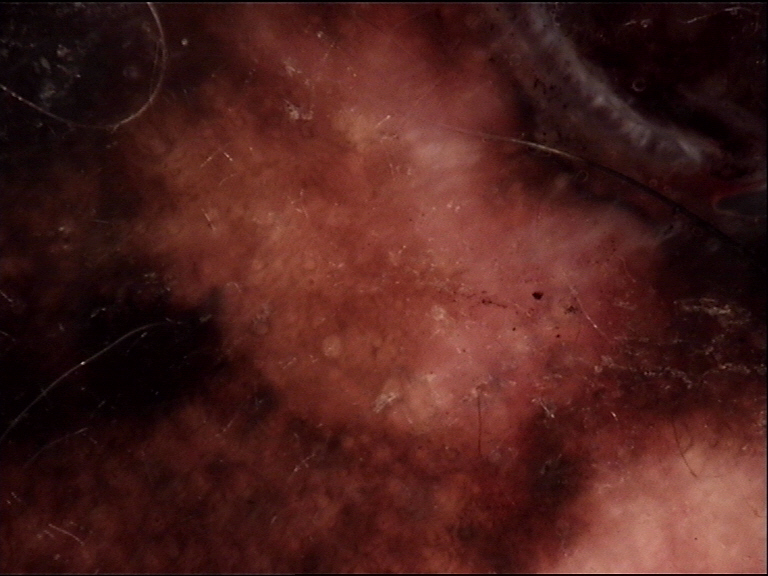Diagnosis:
Confirmed on histopathology as a lentigo maligna melanoma.